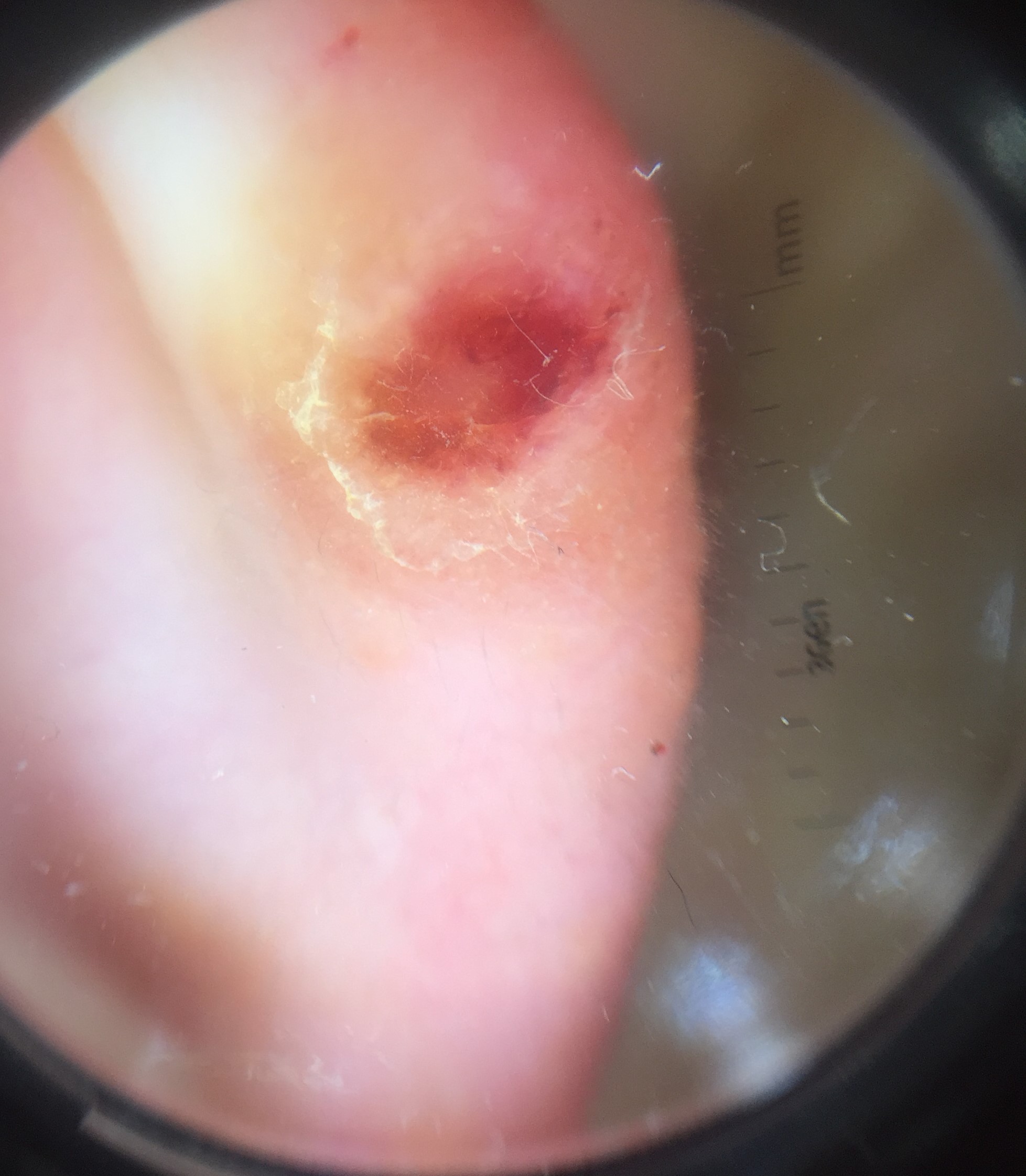<case>
<diagnosis>
<name>squamous cell carcinoma</name>
<code>scc</code>
<malignancy>malignant</malignancy>
<super_class>non-melanocytic</super_class>
<confirmation>histopathology</confirmation>
</diagnosis>
</case>